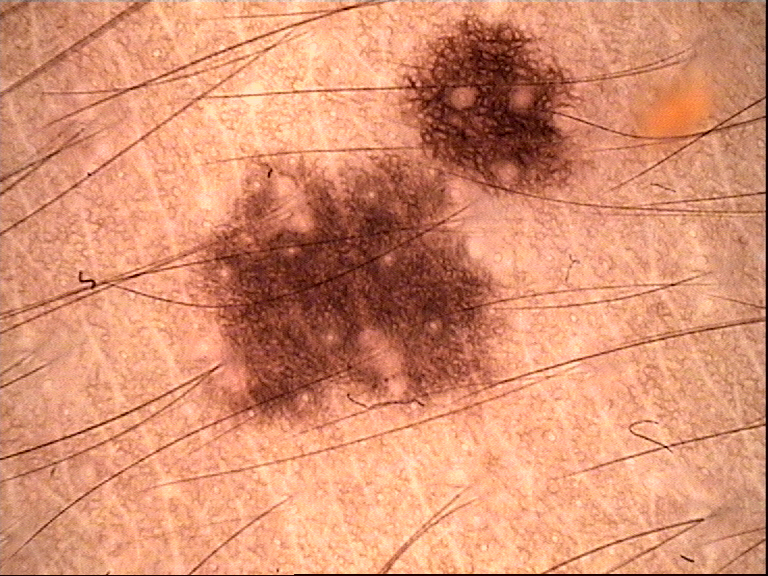image type: dermatoscopy | assessment: dysplastic junctional nevus (expert consensus).